A dermoscopic photograph of a skin lesion:
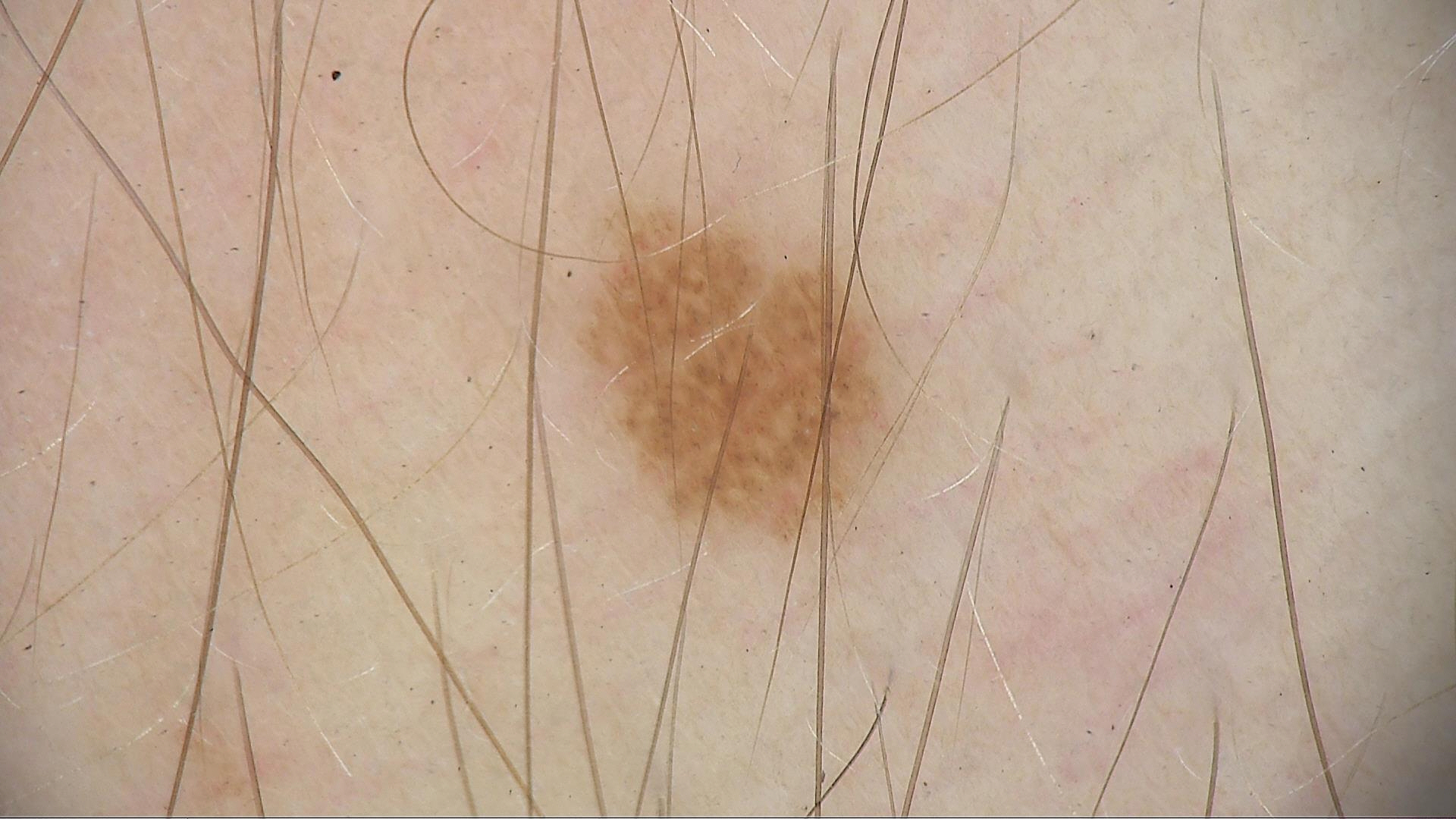Findings:
– label: dysplastic junctional nevus (expert consensus)